Present for less than one week; texture is reported as raised or bumpy; the patient reported no systemic symptoms; the photograph was taken at a distance; located on the arm; symptoms reported: itching:
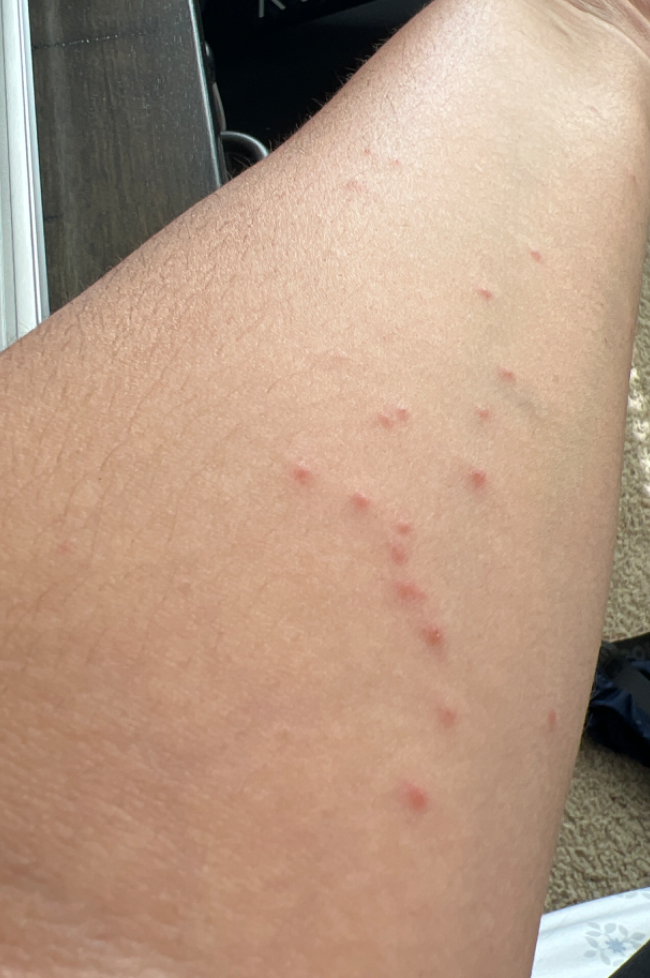  differential:
    leading:
      - Insect Bite
    considered:
      - Hypersensitivity
    unlikely:
      - Eczema